Collected as part of a research study, without a referral diagnosis. By self-report, immunosuppression, a personal history of skin cancer, a family history of skin cancer, no sunbed use, and no prior organ transplant. A male patient aged 65. The patient says their skin reddens painfully with sun exposure — 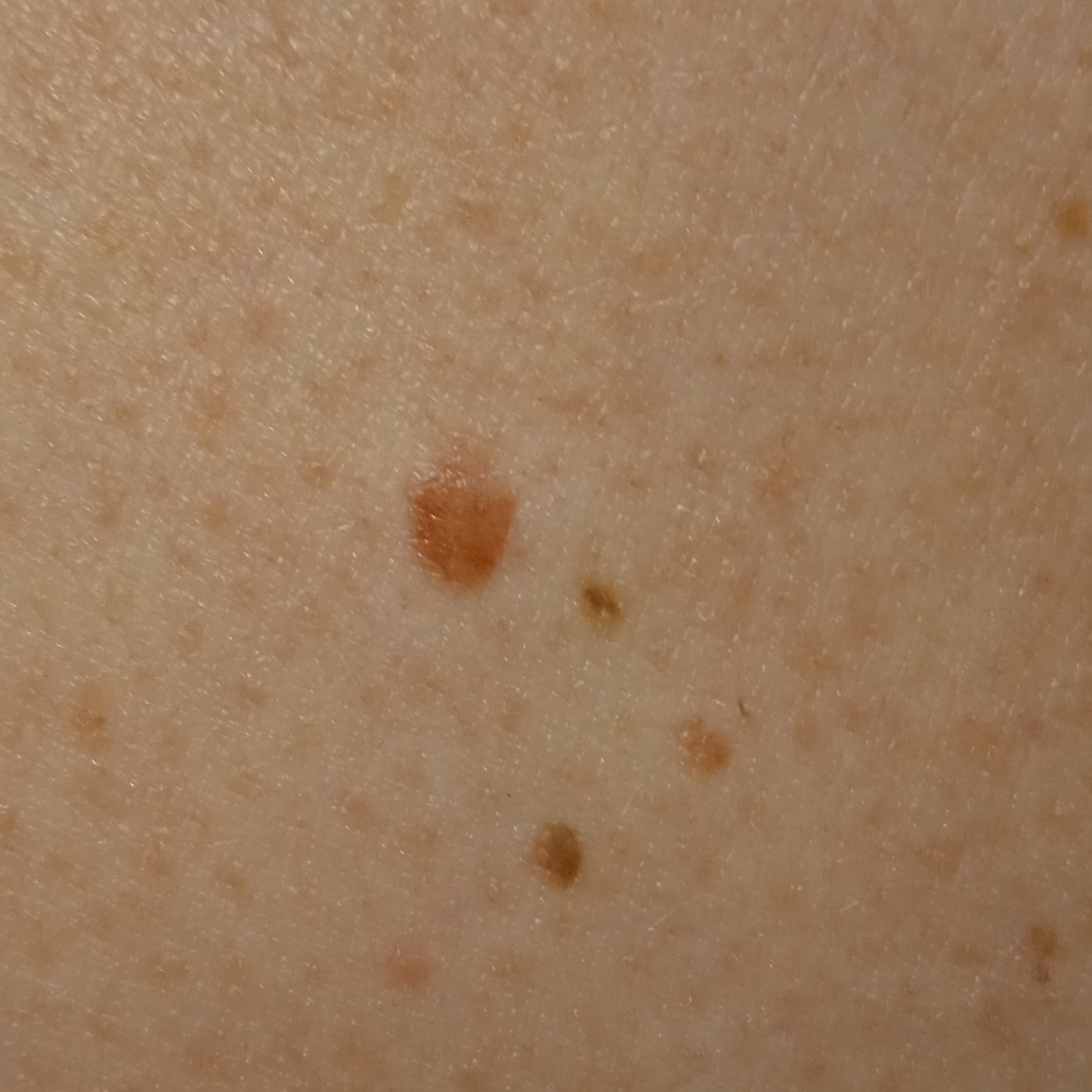site: the back; size: 4.4 mm; assessment: melanocytic nevus (dermatologist consensus).